Located on the leg; this image was taken at an angle — 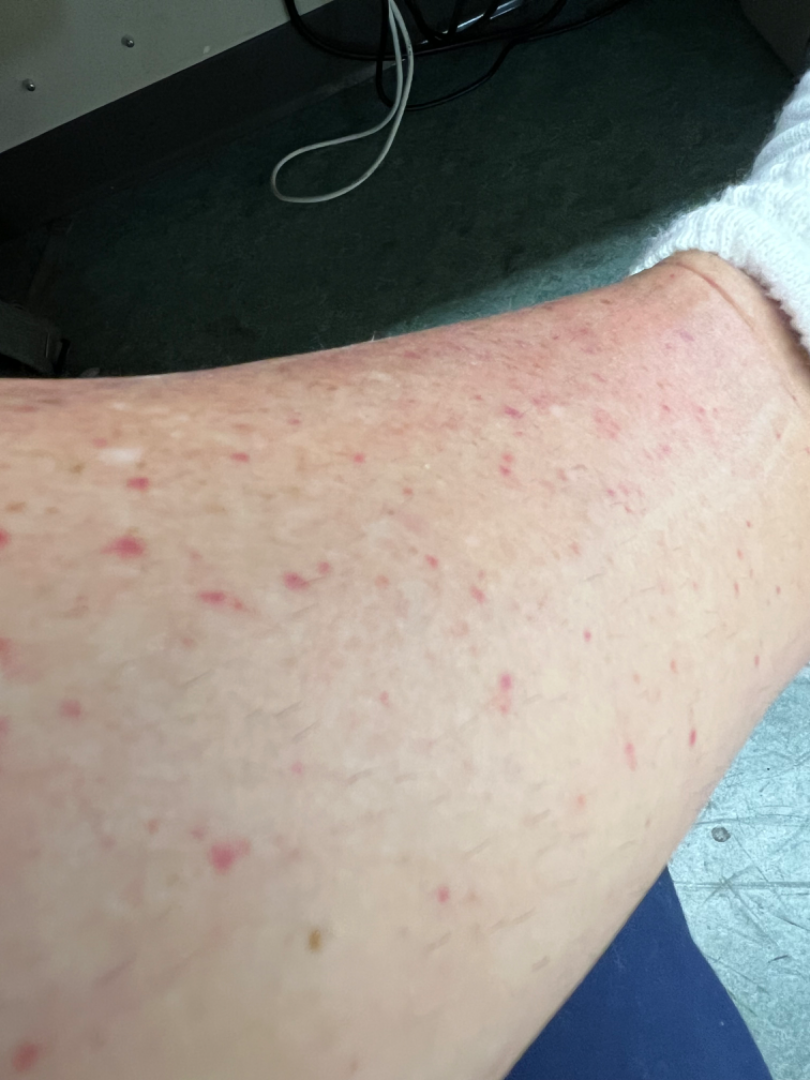The skin findings could not be characterized from the image.